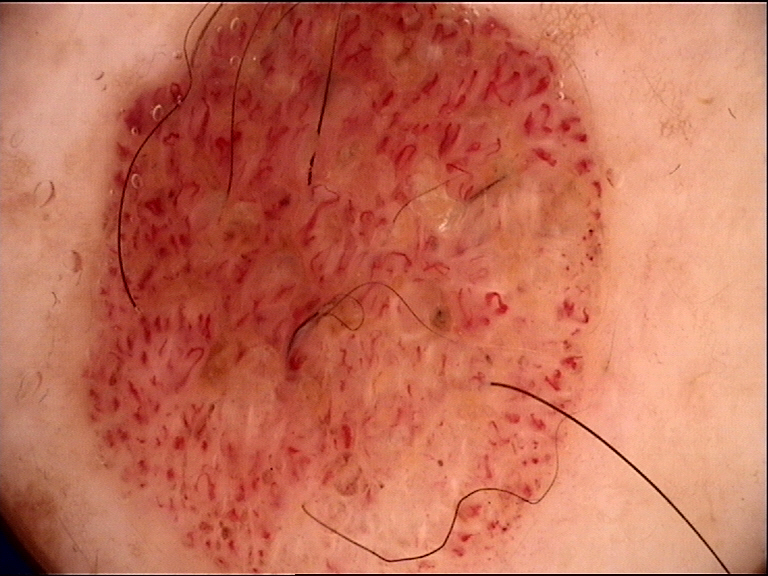image type = dermatoscopy
category = banal
diagnosis = dermal nevus (expert consensus)